This is a close-up image · female patient, age 40–49 · the arm and leg are involved: 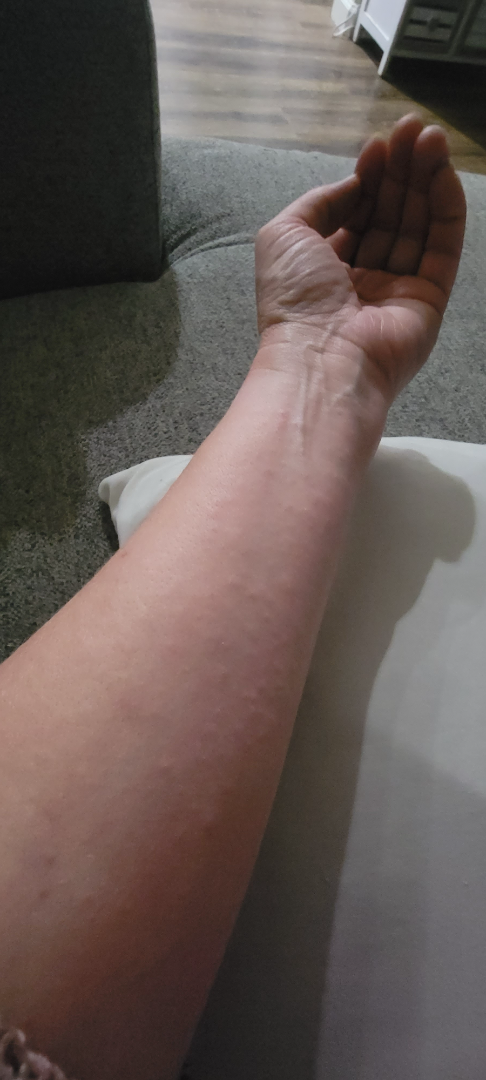Allergic Contact Dermatitis (primary); Lichenoid myxedema (considered); Viral Exanthem (unlikely).